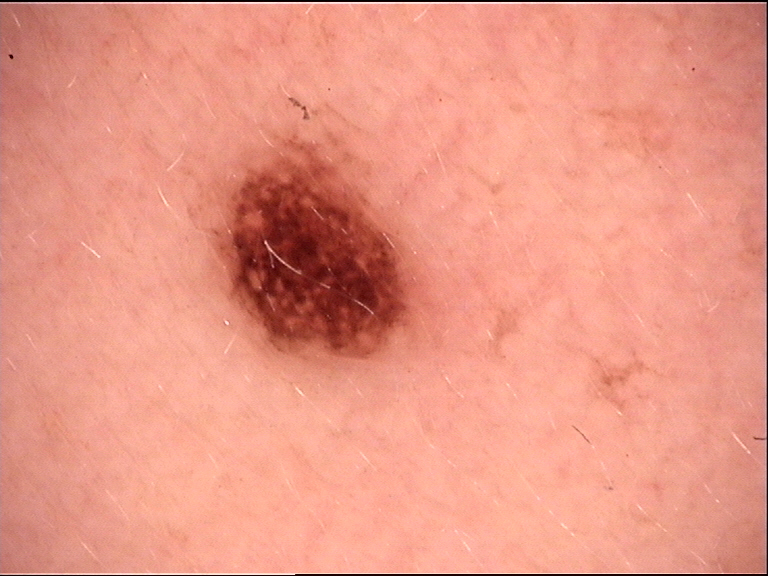Consistent with a compound nevus.